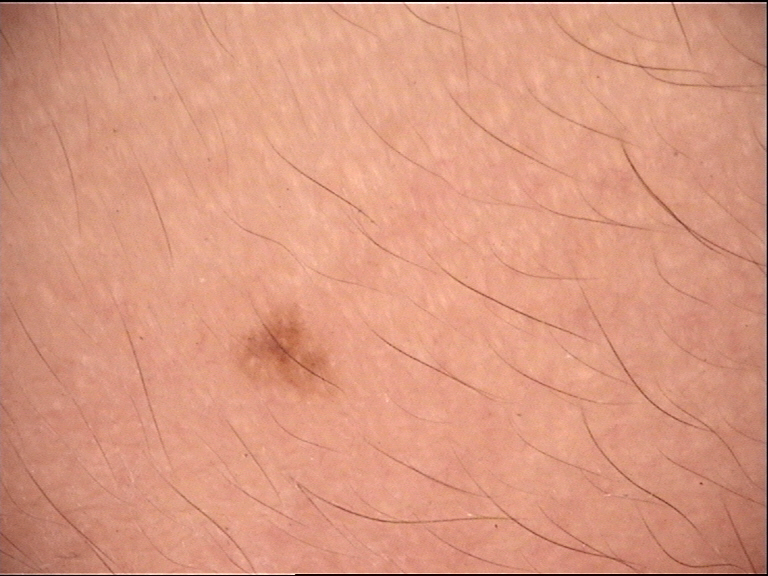Consistent with a junctional nevus.